A macroscopic clinical photograph of a skin lesion · a female subject 59 years old:
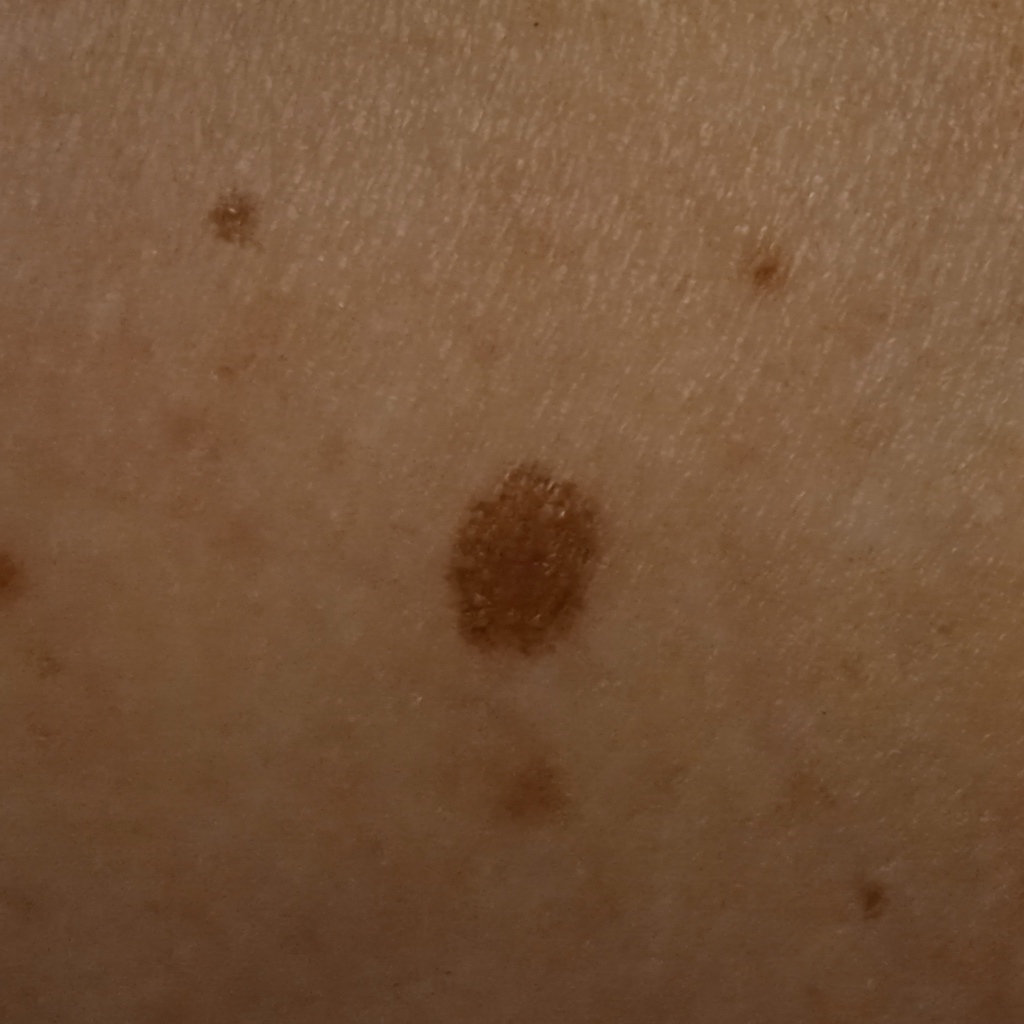diagnostic label = atypical (dysplastic) nevus — biopsy-proven.